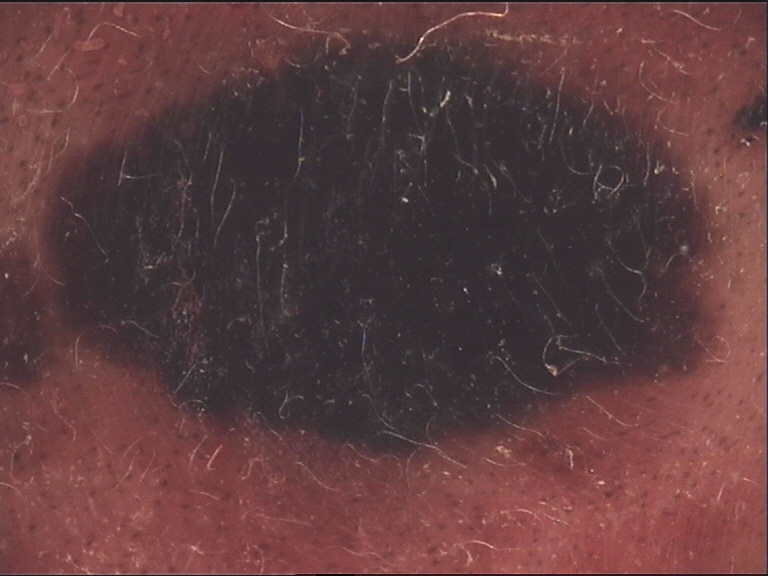lesion_type:
  main_class: banal
  pattern: compound
diagnosis:
  name: congenital compound nevus
  code: ccb
  malignancy: benign
  super_class: melanocytic
  confirmation: expert consensus